Female subject, age 60–69 · the affected area is the top or side of the foot · the patient reports the lesion is raised or bumpy · self-categorized by the patient as a rash · reported lesion symptoms include bothersome appearance · the patient reports associated joint pain · the photo was captured at a distance — 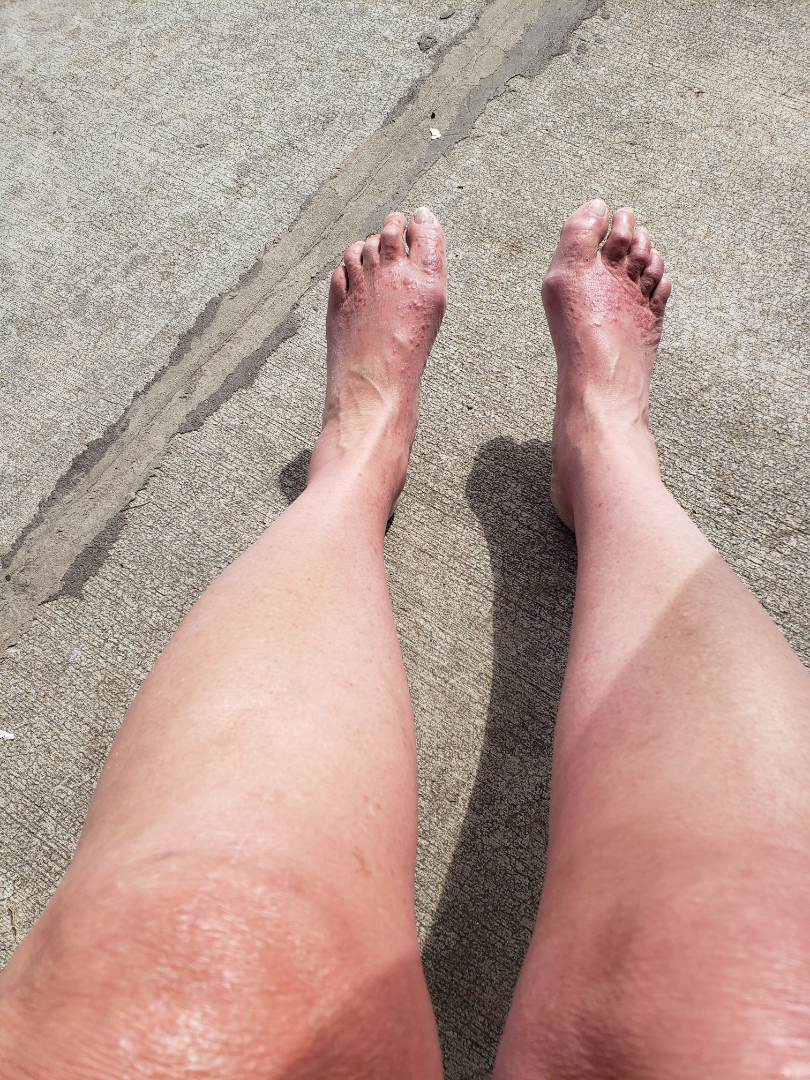Q: What is the dermatologist's impression?
A: most consistent with Lichen planus/lichenoid eruption